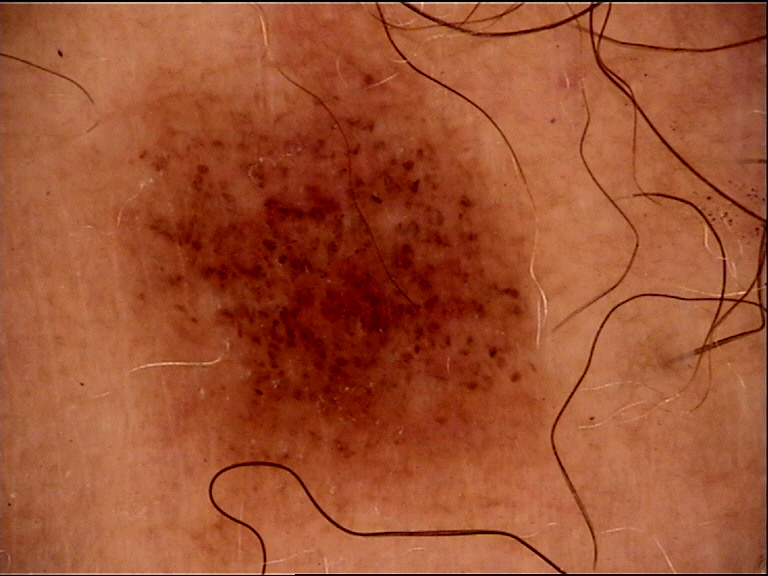| feature | finding |
|---|---|
| diagnostic label | dysplastic junctional nevus (expert consensus) |